The lesion is associated with itching · reported duration is one to four weeks · the patient indicates the lesion is raised or bumpy · female subject, age 30–39 · the photo was captured at an angle — 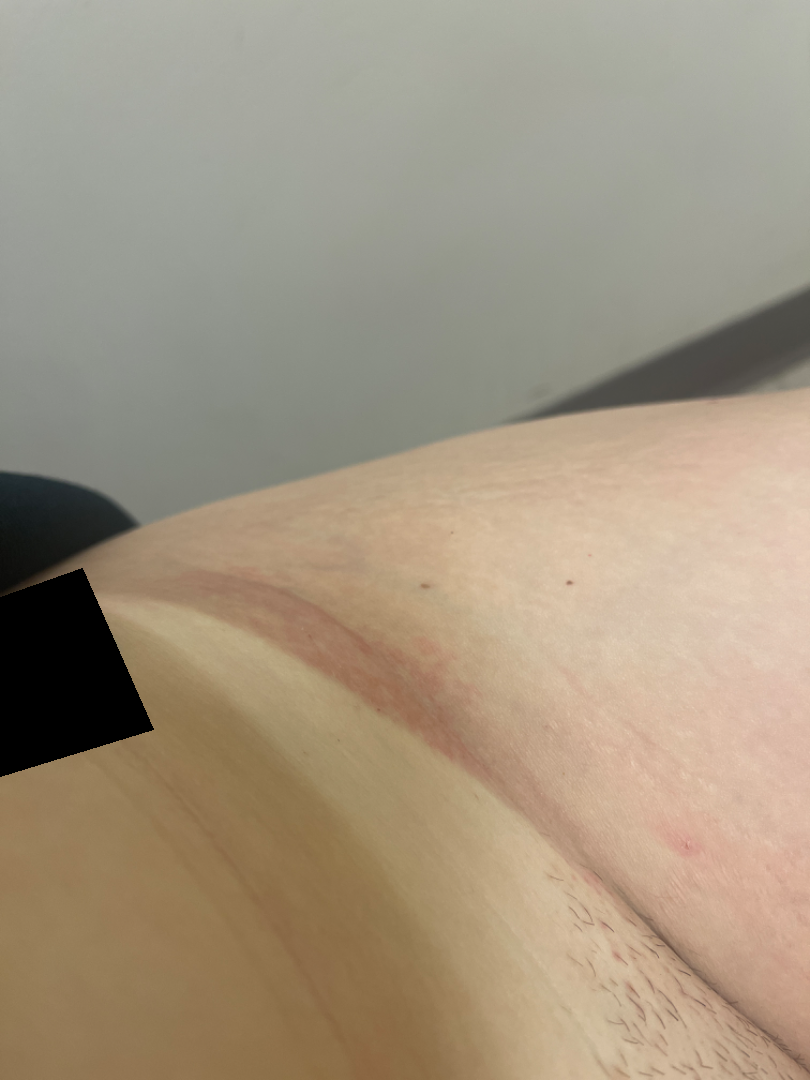Q: What is the dermatologist's impression?
A: the differential is split between Intertrigo and Allergic Contact Dermatitis; possibly Irritant Contact Dermatitis